This is a dermoscopic photograph of a skin lesion — 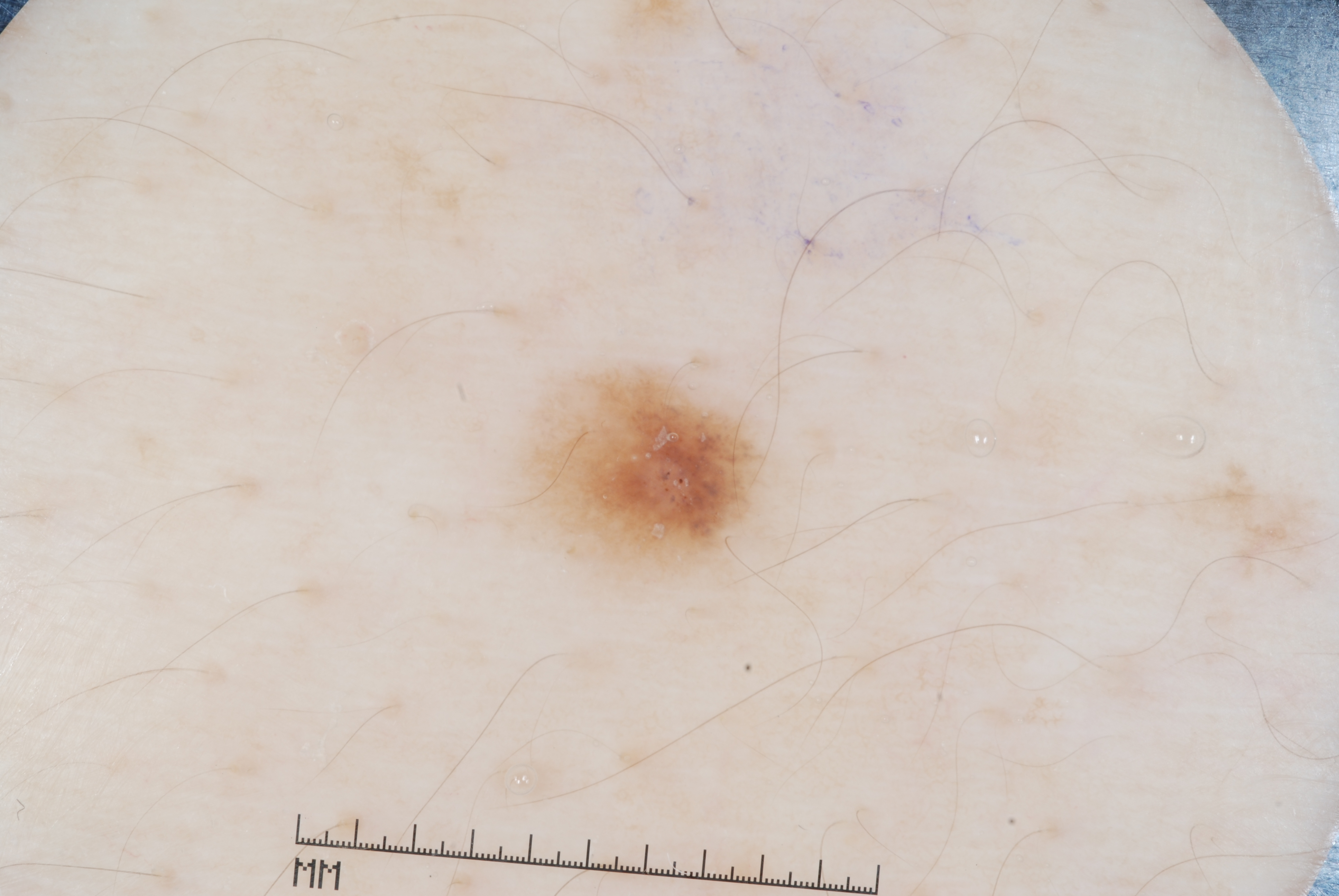Case summary:
* bounding box: x1=513 y1=365 x2=764 y2=581
* impression: a melanocytic nevus